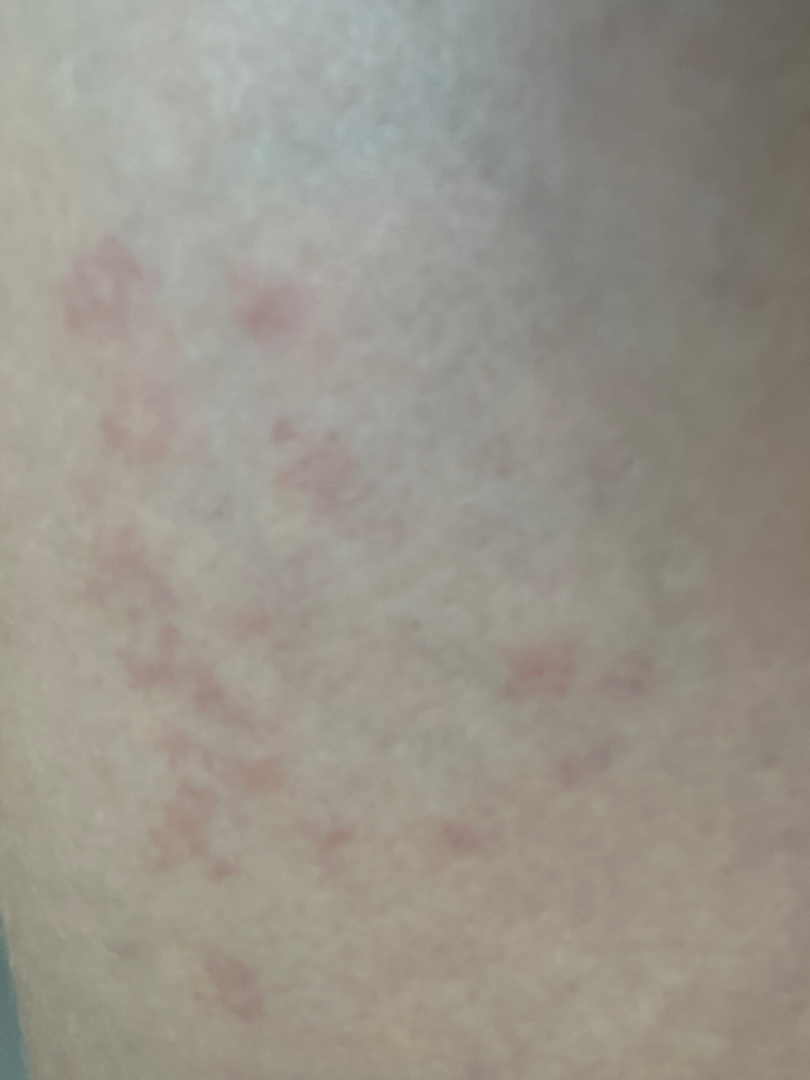Most likely Hypersensitivity.